The affected area is the front of the torso, the photo was captured at a distance.
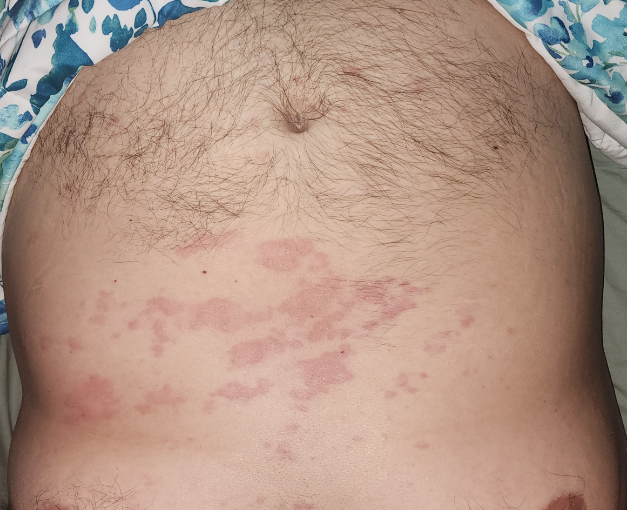Findings:
– texture: raised or bumpy
– skin tone: Fitzpatrick III; lay graders estimated 3 on the Monk Skin Tone
– onset: about one day
– patient describes the issue as: a rash
– dermatologist impression: the leading consideration is Urticaria